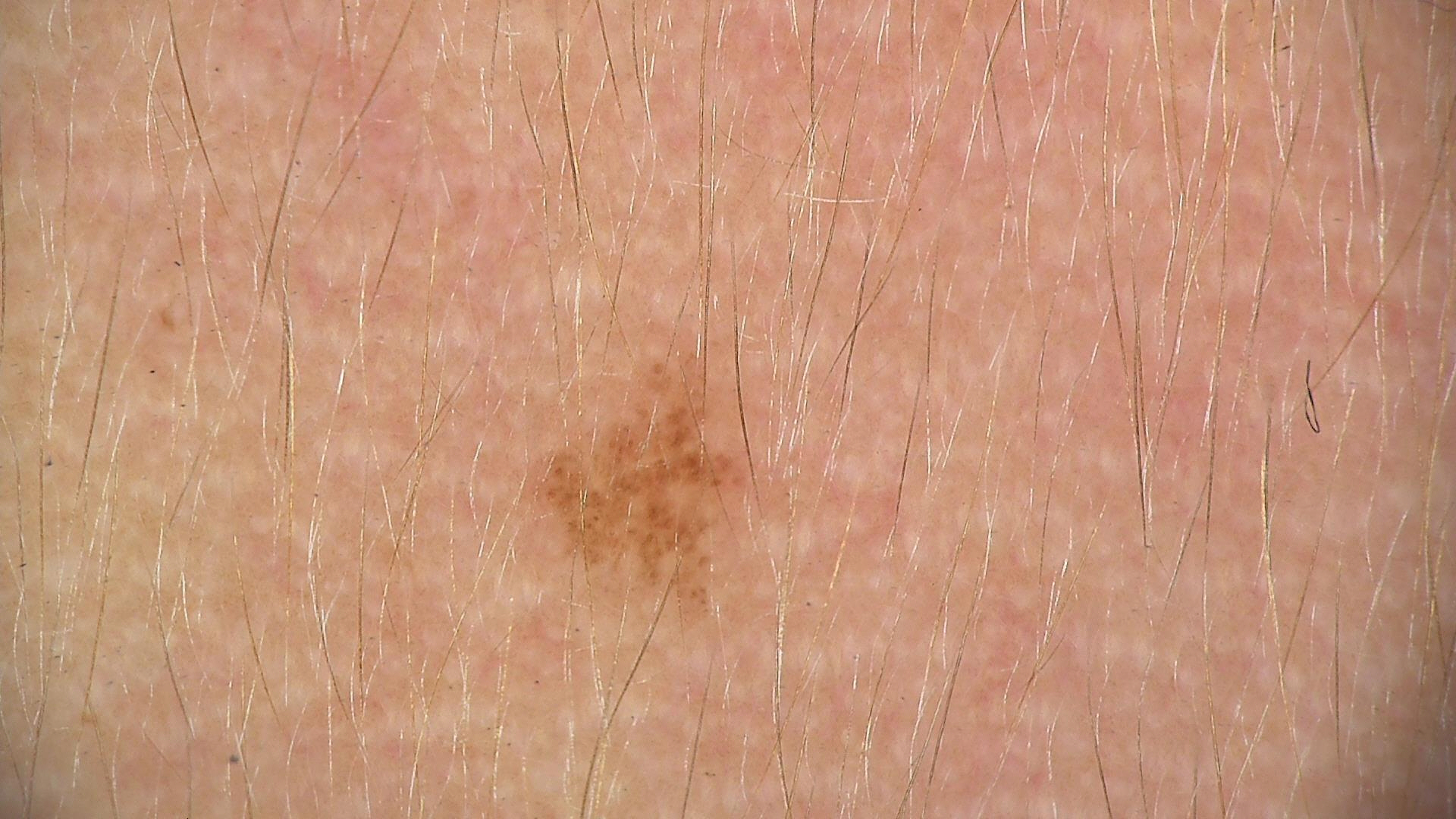The diagnosis was a dysplastic junctional nevus.